Located on the arm. The patient is a female aged 40–49. An image taken at an angle — 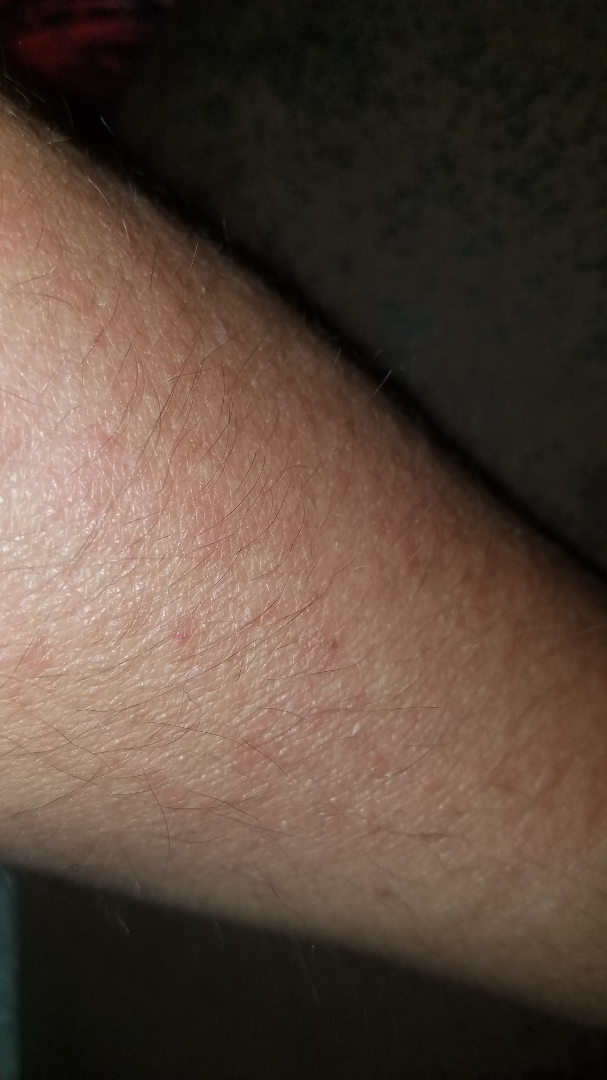assessment = indeterminate
skin tone = Fitzpatrick skin type III
onset = less than one week
lesion symptoms = itching and burning
patient's own categorization = a rash